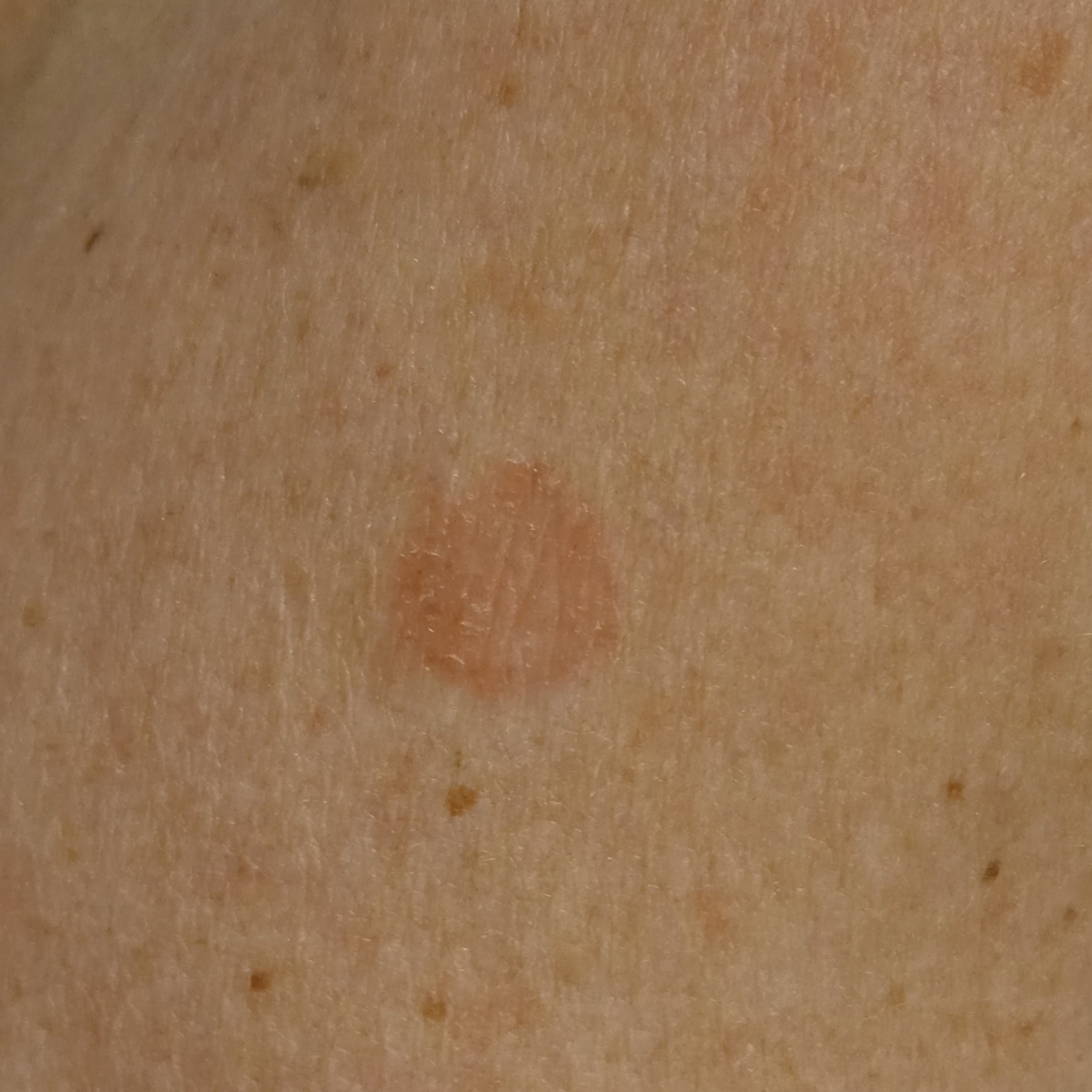relevant history = a prior organ transplant, immunosuppression; nevus count = a moderate number of melanocytic nevi; image type = clinical photo; patient = female, 55 years old; anatomic site = an arm; size = 13.2 mm; diagnosis = basal cell carcinoma (dermatologist consensus).